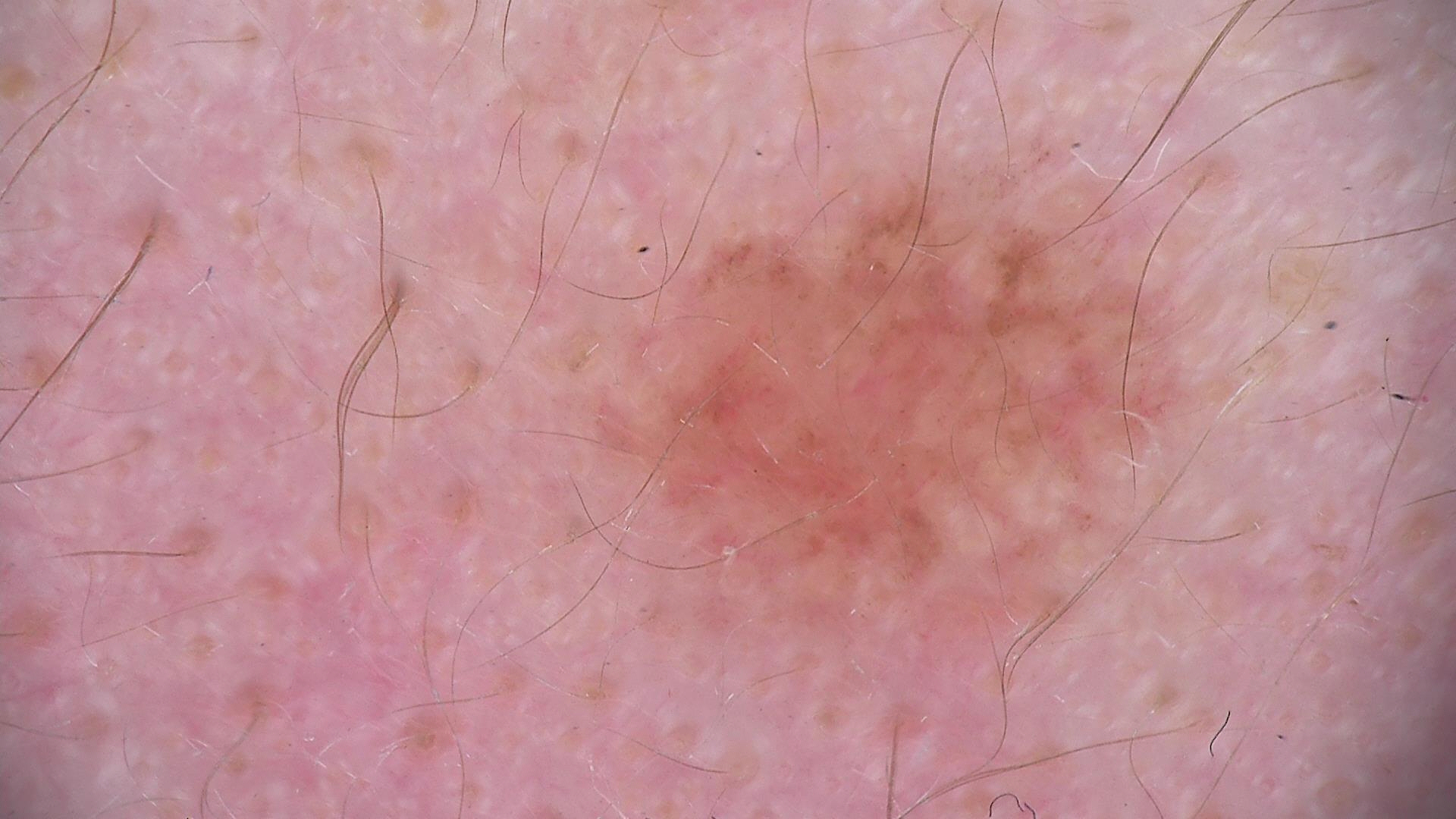image type = dermatoscopy; classification = banal; class = compound nevus (expert consensus).